Female contributor, age 18–29. The affected area is the leg, arm and head or neck. This is a close-up image — 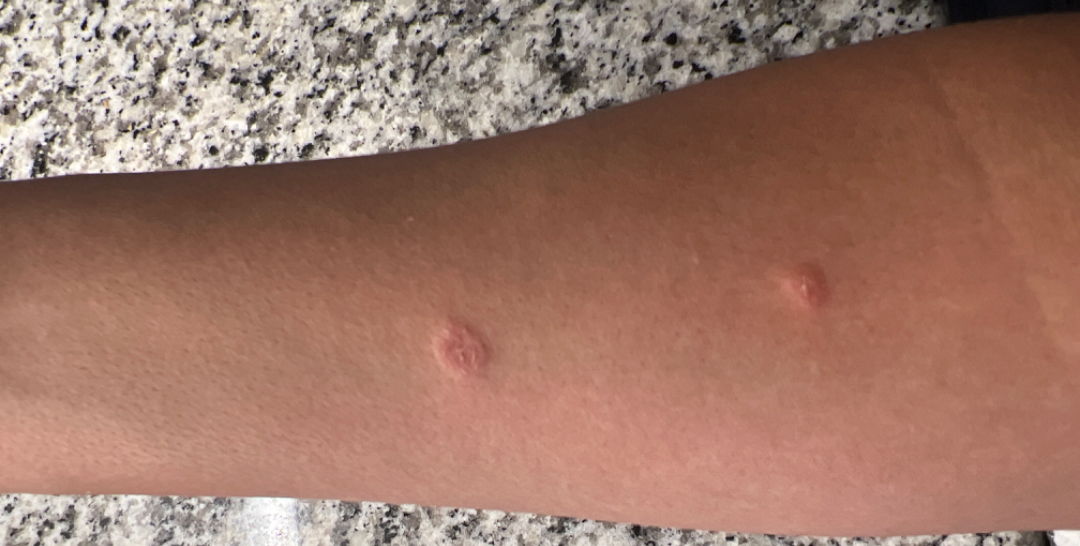Symptoms reported: itching and bothersome appearance.
The patient described the issue as a rash.
No associated systemic symptoms reported.
In keeping with Insect Bite.